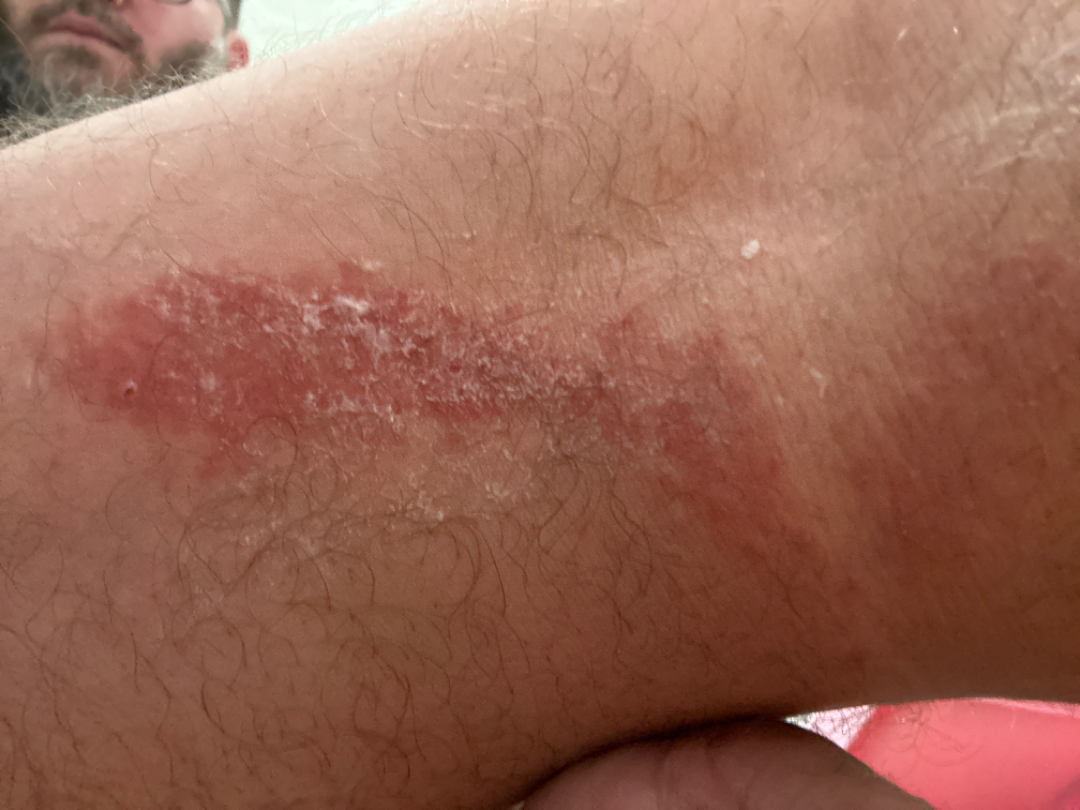Notes:
* assessment · the differential, in no particular order, includes Psoriasis and Eczema; less probable is Lichen Simplex Chronicus